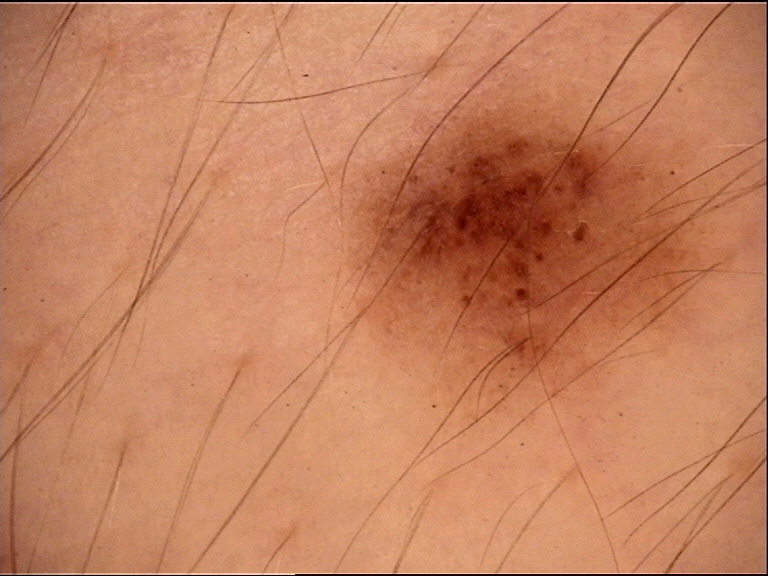The diagnostic label was a junctional nevus.